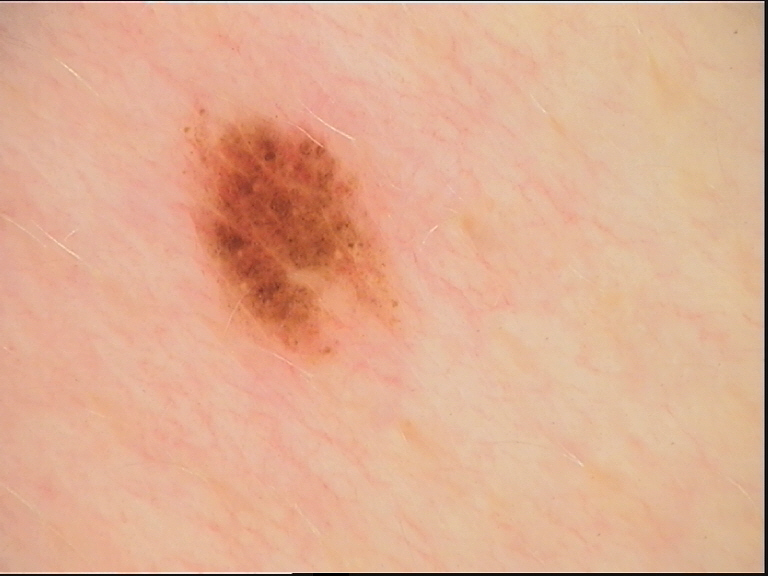The diagnostic label was a dysplastic compound nevus.